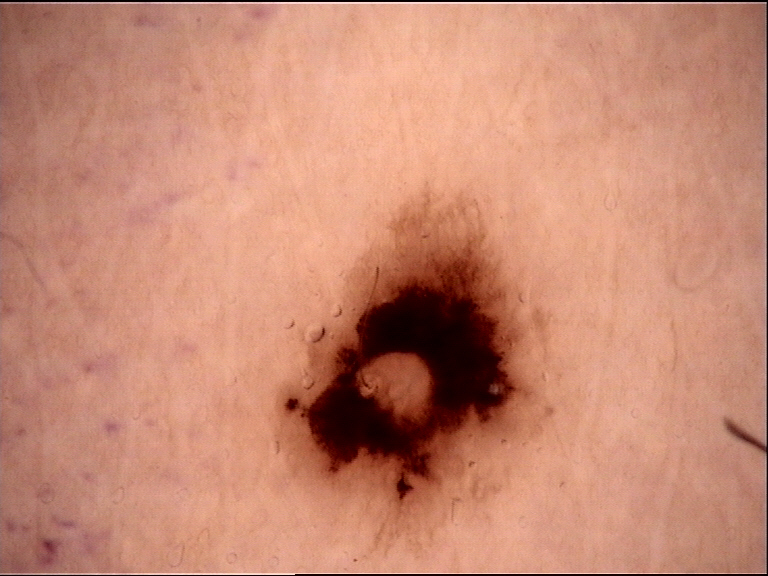Consistent with a dysplastic junctional nevus.